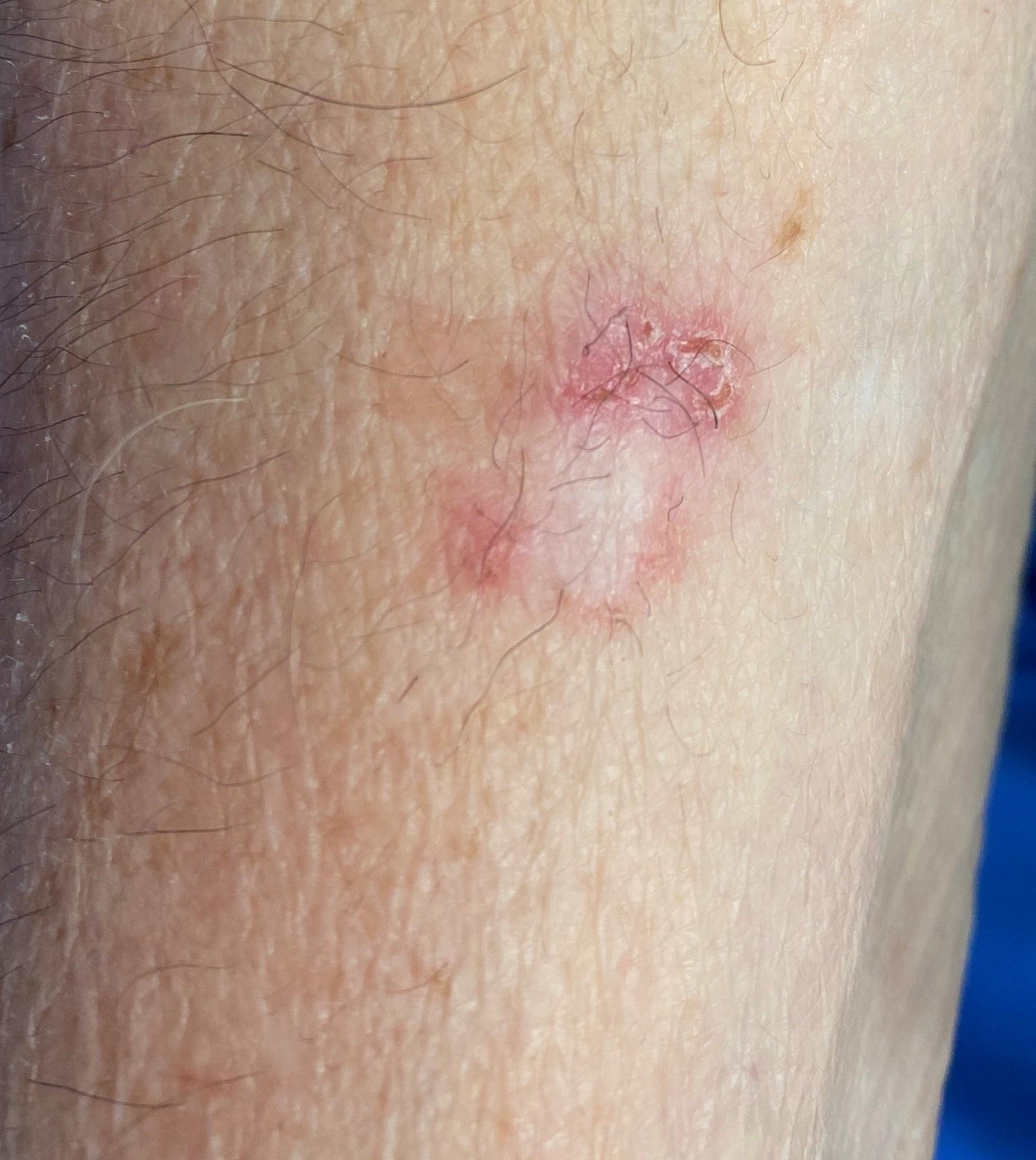Fitzpatrick skin type II. A wide-field clinical photograph of a skin lesion. A female patient approximately 80 years of age. The lesion was found on an upper extremity. Histopathological examination showed a tumor of follicular differentiation — a basal cell carcinoma.